A dermoscopy image of a single skin lesion:
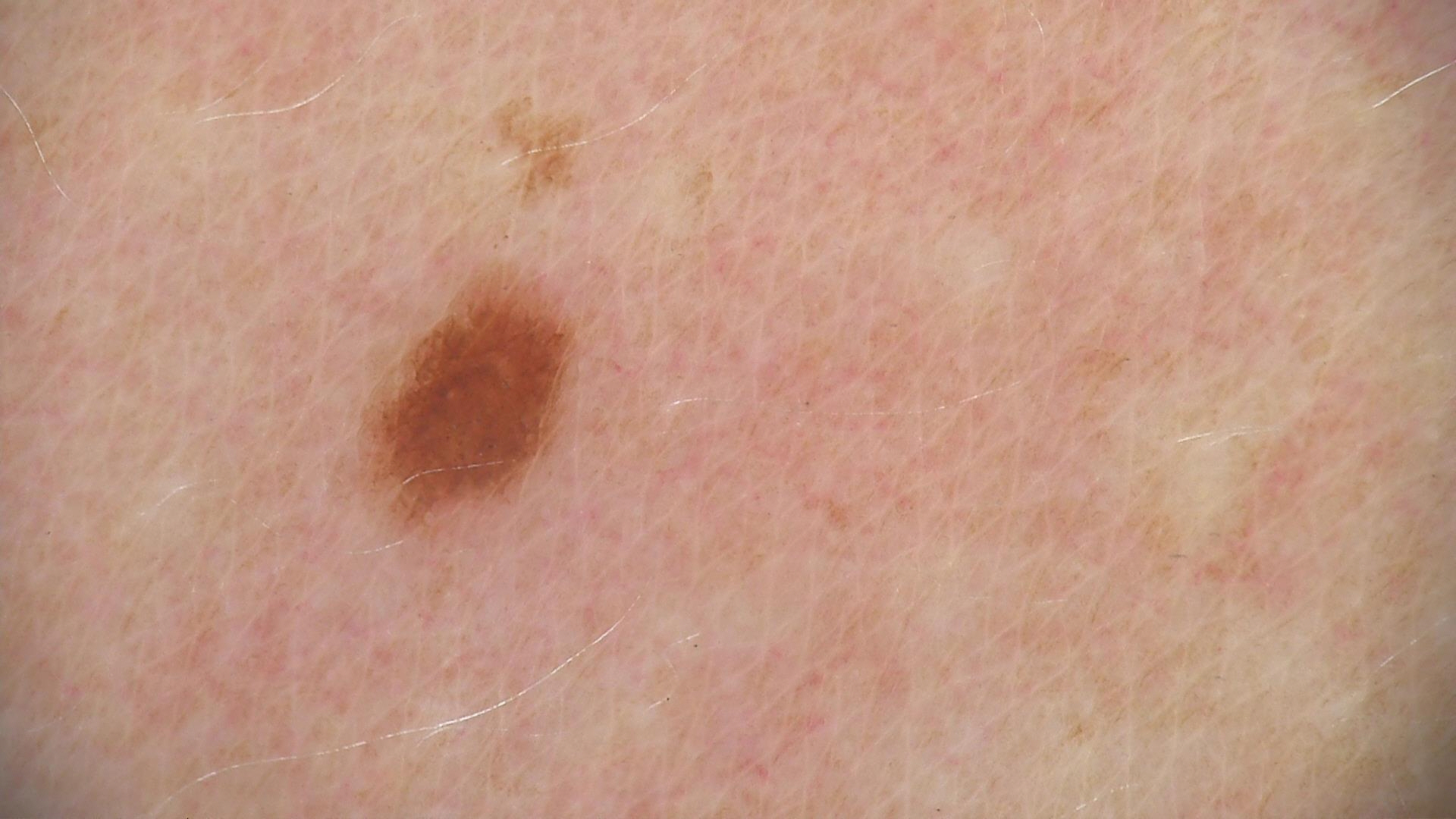* diagnostic label — dysplastic junctional nevus (expert consensus)